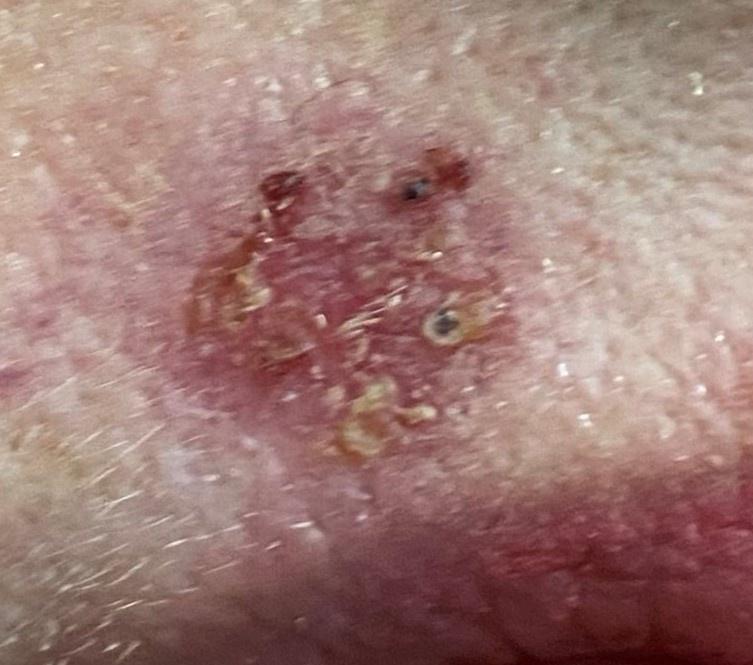| field | value |
|---|---|
| skin type | II |
| image type | clinical photo (overview) |
| patient | female, about 60 years old |
| diagnosis | Basal cell carcinoma (biopsy-proven) |